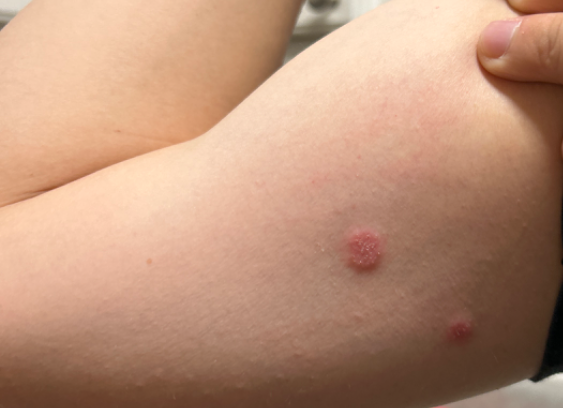Reported duration is less than one week. The lesion is described as raised or bumpy and rough or flaky. Self-categorized by the patient as a rash. The photograph was taken at an angle. On remote review of the image, consistent with Eczema.